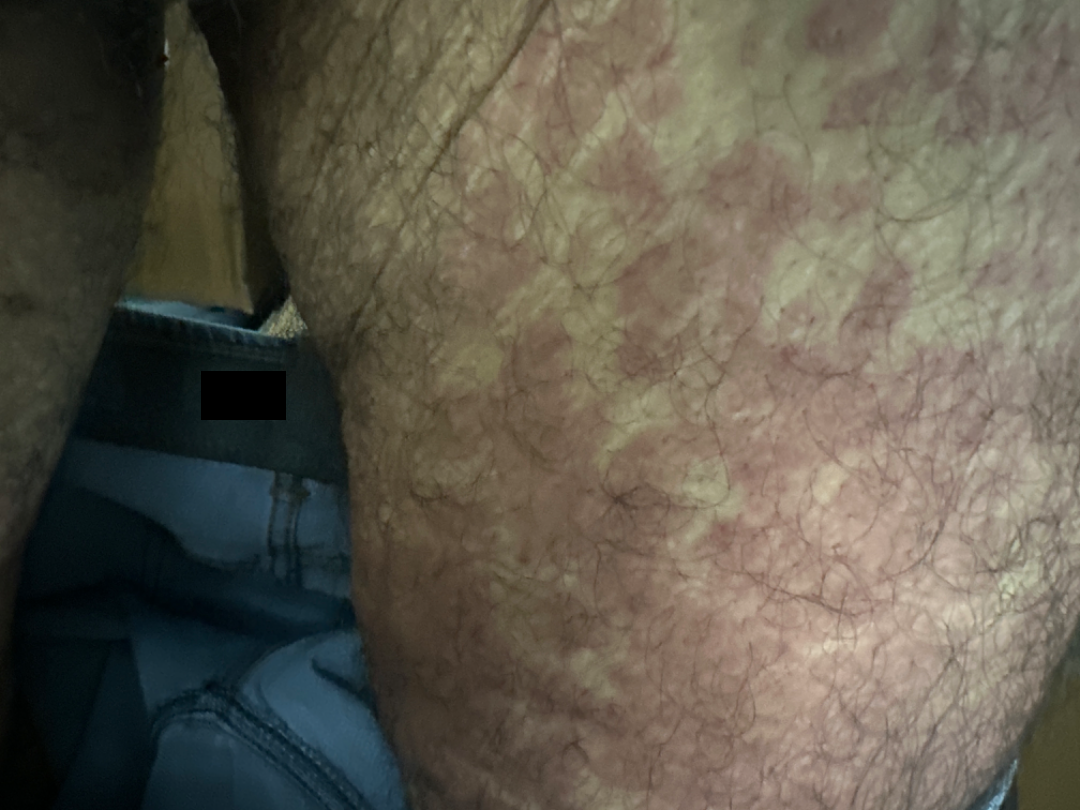The case was indeterminate on photographic review. The affected area is the leg. This is a close-up image. The patient described the issue as a rash. FST IV; non-clinician graders estimated Monk skin tone scale 3 or 7 (two reviewer pools disagreed). Reported duration is less than one week.